Numerous moles by the patient's own estimate. By self-report, a family history of skin cancer, immunosuppression, a personal history of skin cancer, no personal history of cancer, and no sunbed use. The patient says their skin reddens painfully with sun exposure. Acquired for a research image collection, with no referral diagnosis. A dermatoscopic image of a skin lesion. A male patient 65 years old.
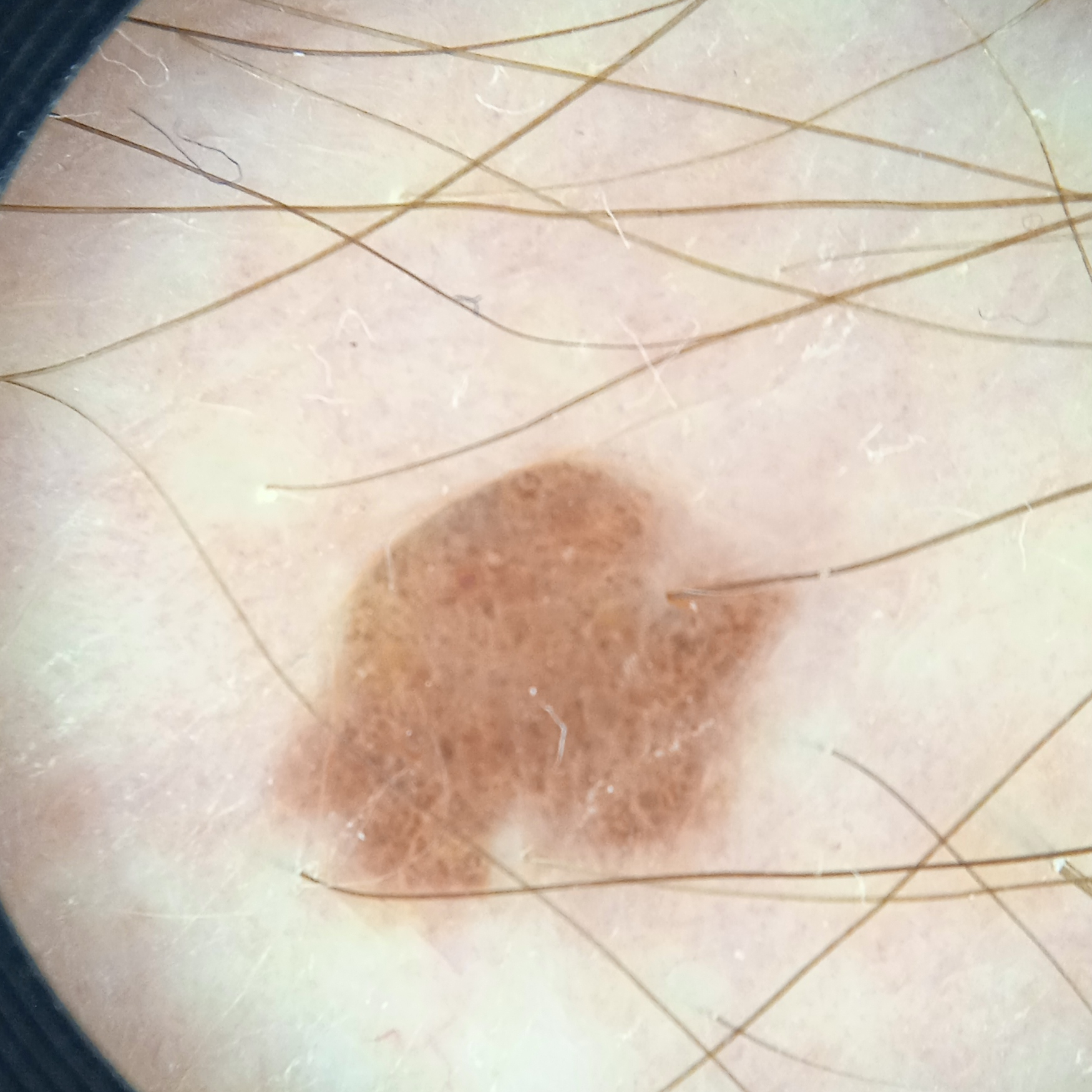anatomic site: an arm; diagnostic label: melanocytic nevus (dermatologist consensus).